A dermoscopic photograph of a skin lesion.
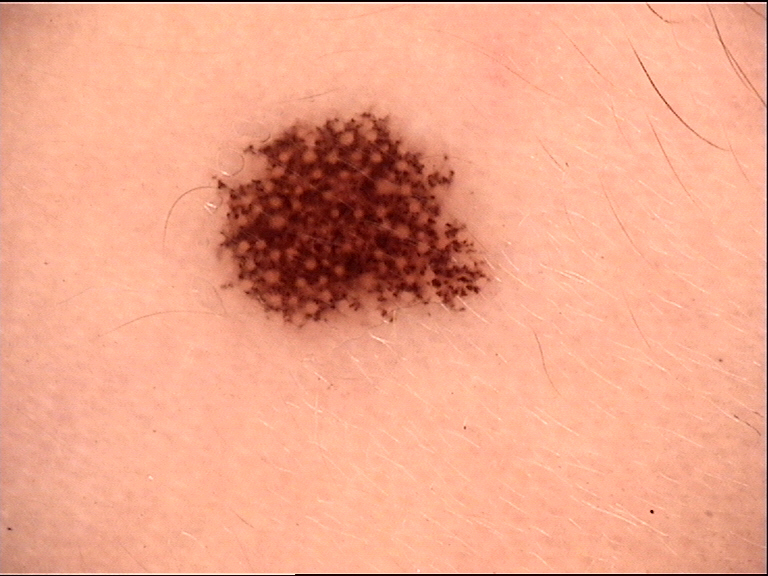The diagnosis was a dysplastic junctional nevus.